Reported duration is more than one year. The subject is a female aged 30–39. Self-categorized by the patient as a rash. The photo was captured at an angle. Self-reported Fitzpatrick II.
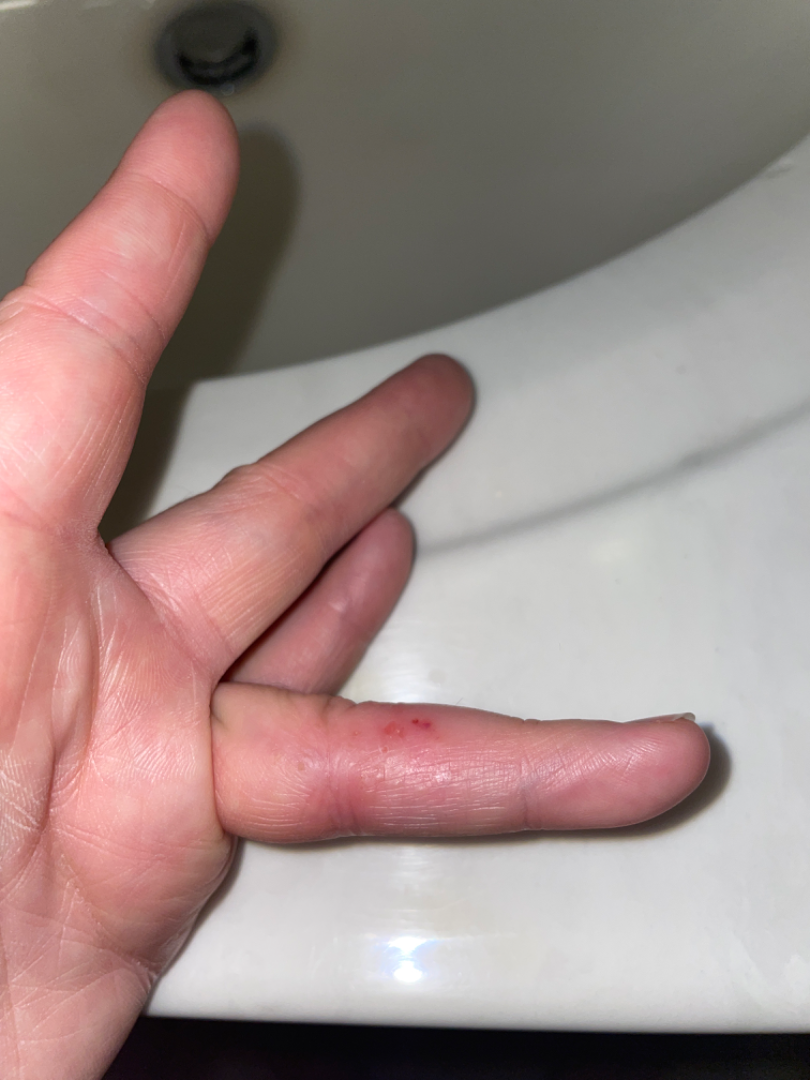The condition could not be reliably identified from the image.